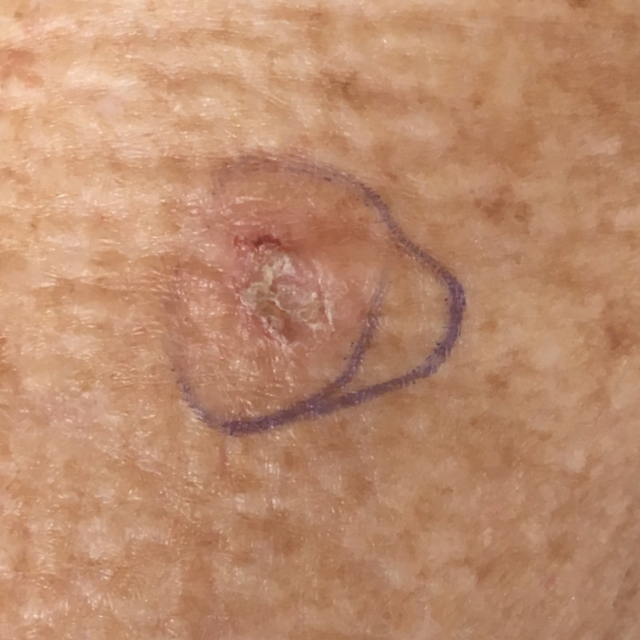Q: Patient demographics?
A: age 77
Q: What kind of image is this?
A: clinical photo
Q: What is the anatomic site?
A: a forearm
Q: What does the patient describe?
A: no bleeding
Q: What was the clinical impression?
A: actinic keratosis (clinical consensus)